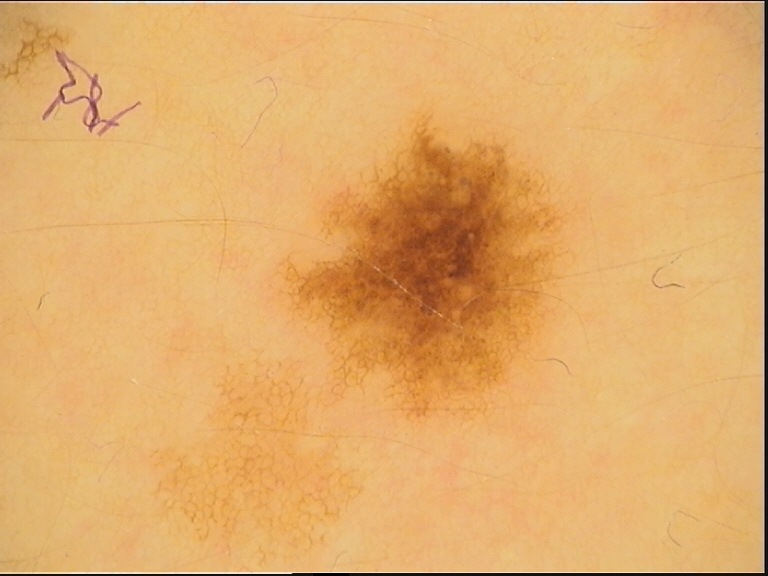Dermoscopy of a skin lesion. The diagnosis was a benign lesion — a dysplastic junctional nevus.